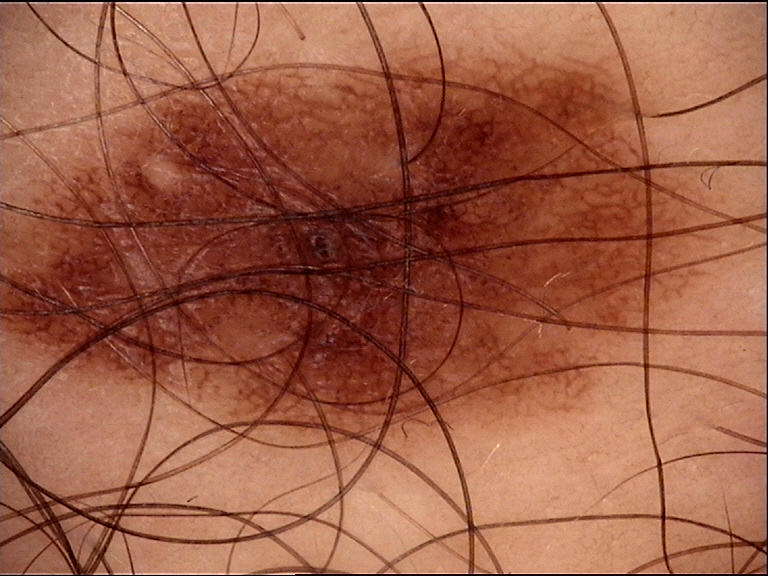{"image": "dermatoscopy", "diagnosis": {"name": "dysplastic junctional nevus", "code": "jd", "malignancy": "benign", "super_class": "melanocytic", "confirmation": "expert consensus"}}